Recorded as Fitzpatrick phototype II. The chart notes prior skin cancer (patient or family) and prior malignancy (patient or family). A female subject in their mid-50s.
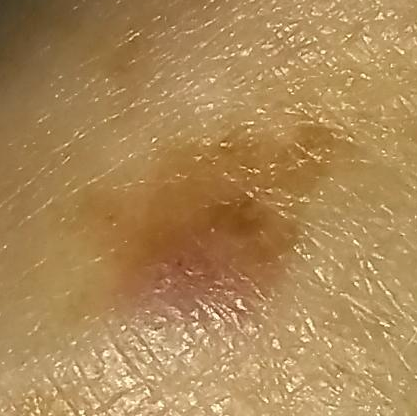region — a hand
lesion size — approx. 7 × 7 mm
symptoms — growth
diagnosis — nevus (clinical consensus)